The photo was captured at a distance — 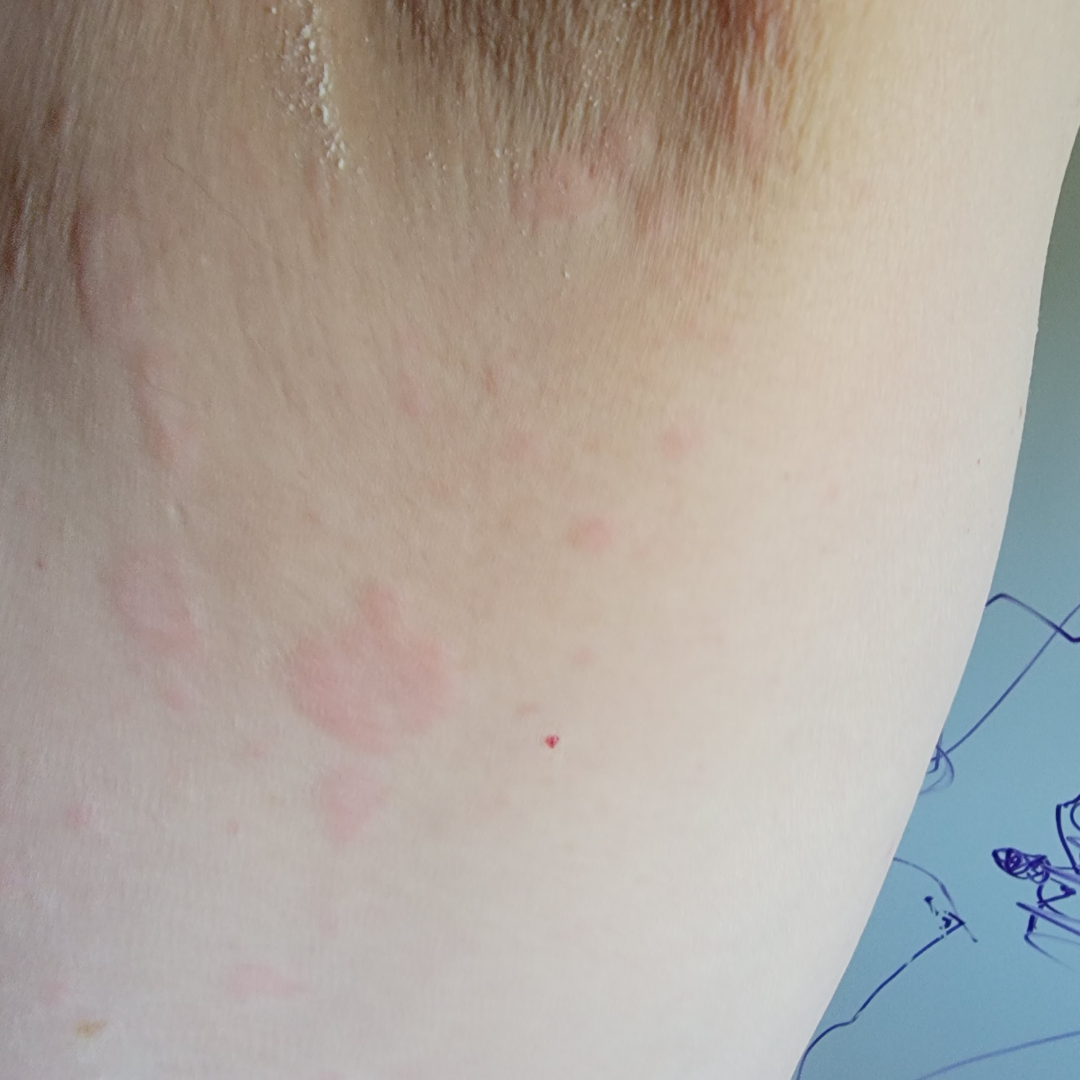Assessment:
The reviewer was unable to grade this case for skin condition.